A smartphone photograph of a skin lesion.
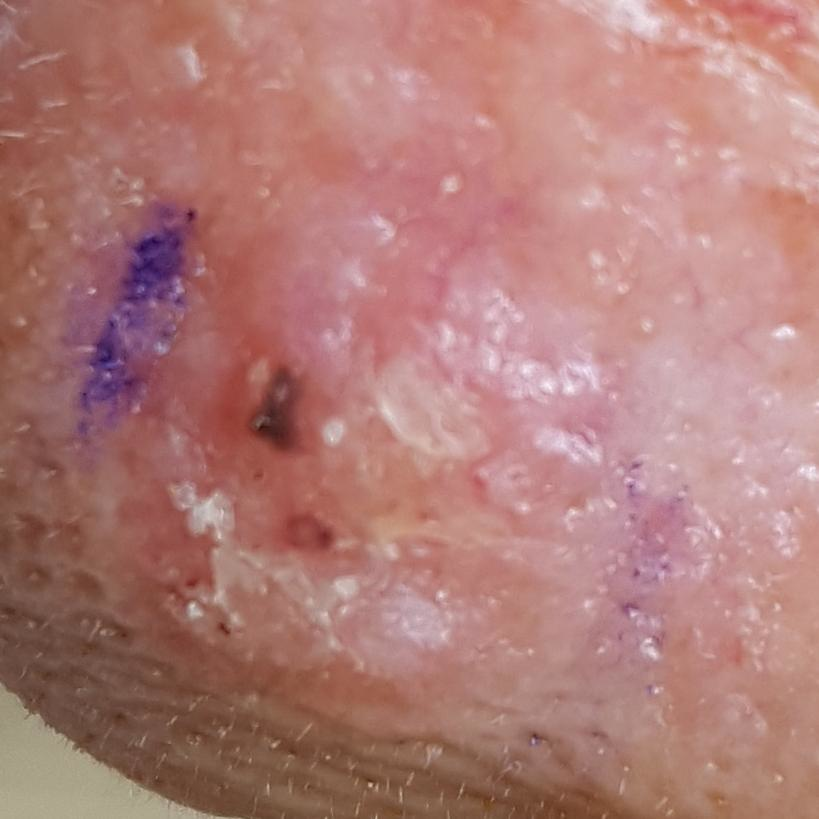  diagnosis:
    name: actinic keratosis
    code: ACK
    malignancy: indeterminate
    confirmation: histopathology